A dermoscopy image of a single skin lesion:
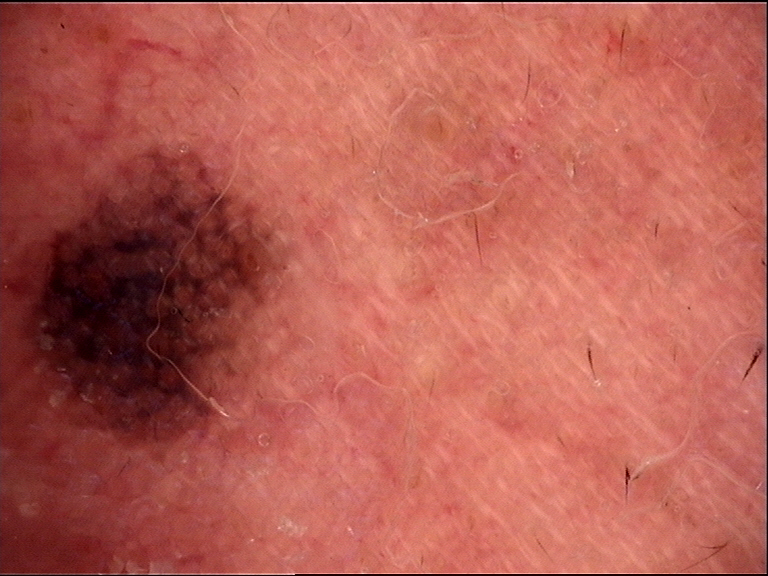subtype = banal
label = compound nevus (expert consensus)